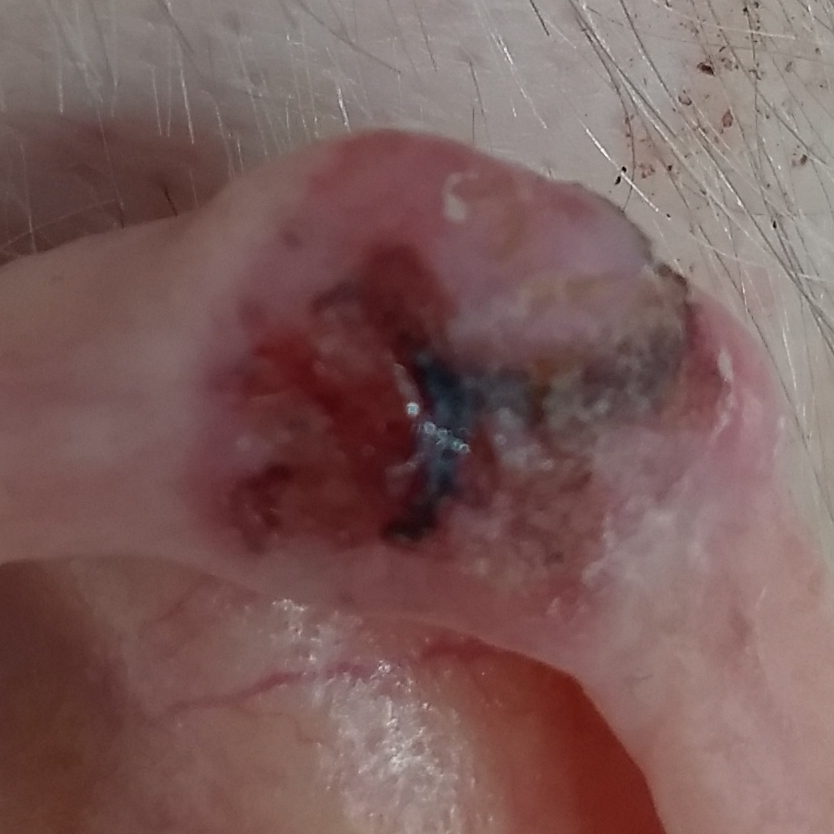A clinical photograph showing a skin lesion.
A female subject in their late 80s.
The lesion is on an ear.
Histopathological examination showed a basal cell carcinoma.